An image taken at an angle.
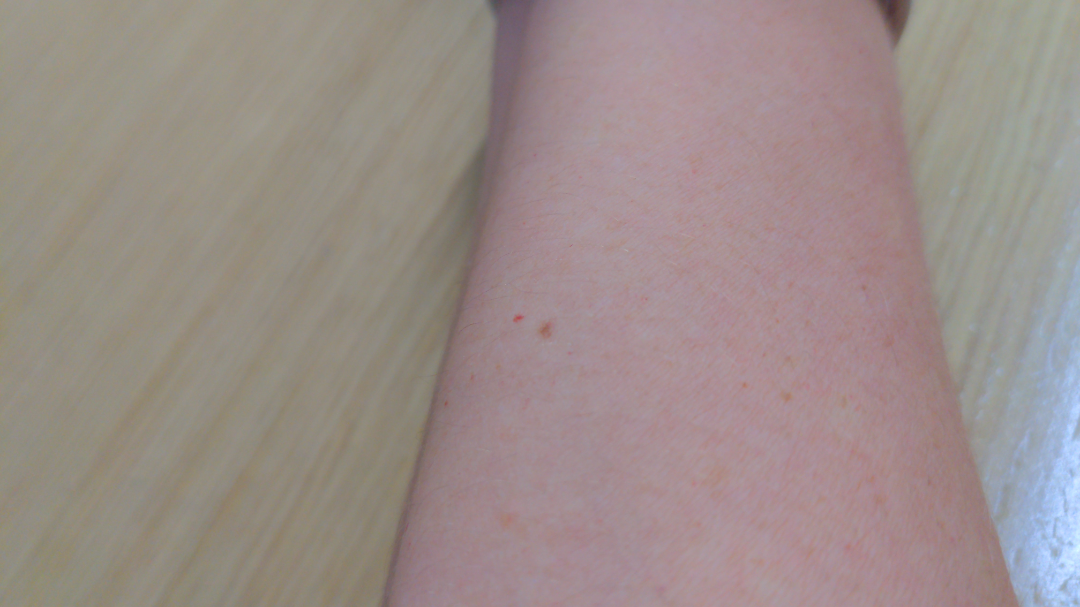Drug Rash and Hypersensitivity were each considered, in no particular order.